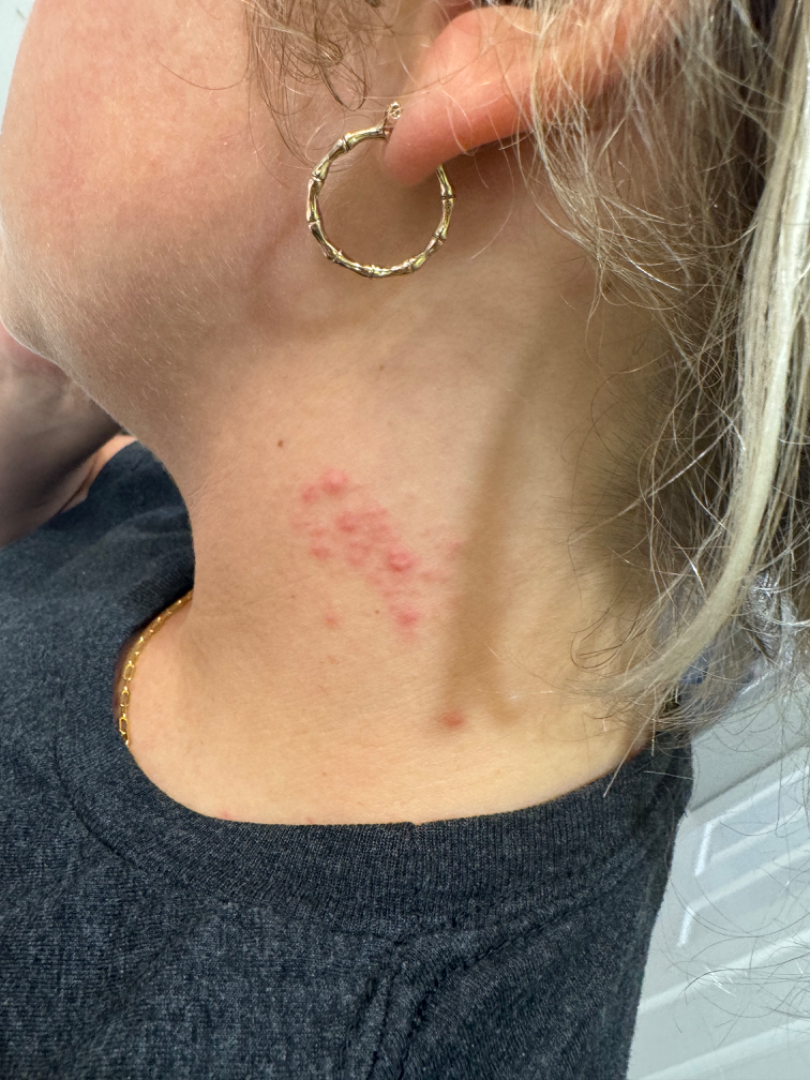Case summary:
- skin tone — Fitzpatrick II
- patient — female, age 18–29
- lesion texture — fluid-filled and raised or bumpy
- site — head or neck
- reported symptoms — bothersome appearance
- image framing — at an angle
- self-categorized as — a rash
- differential diagnosis — single-reviewer assessment: Herpes Zoster, Allergic Contact Dermatitis and Herpes Simplex were considered with similar weight